Acquired for a research image collection, with no referral diagnosis — 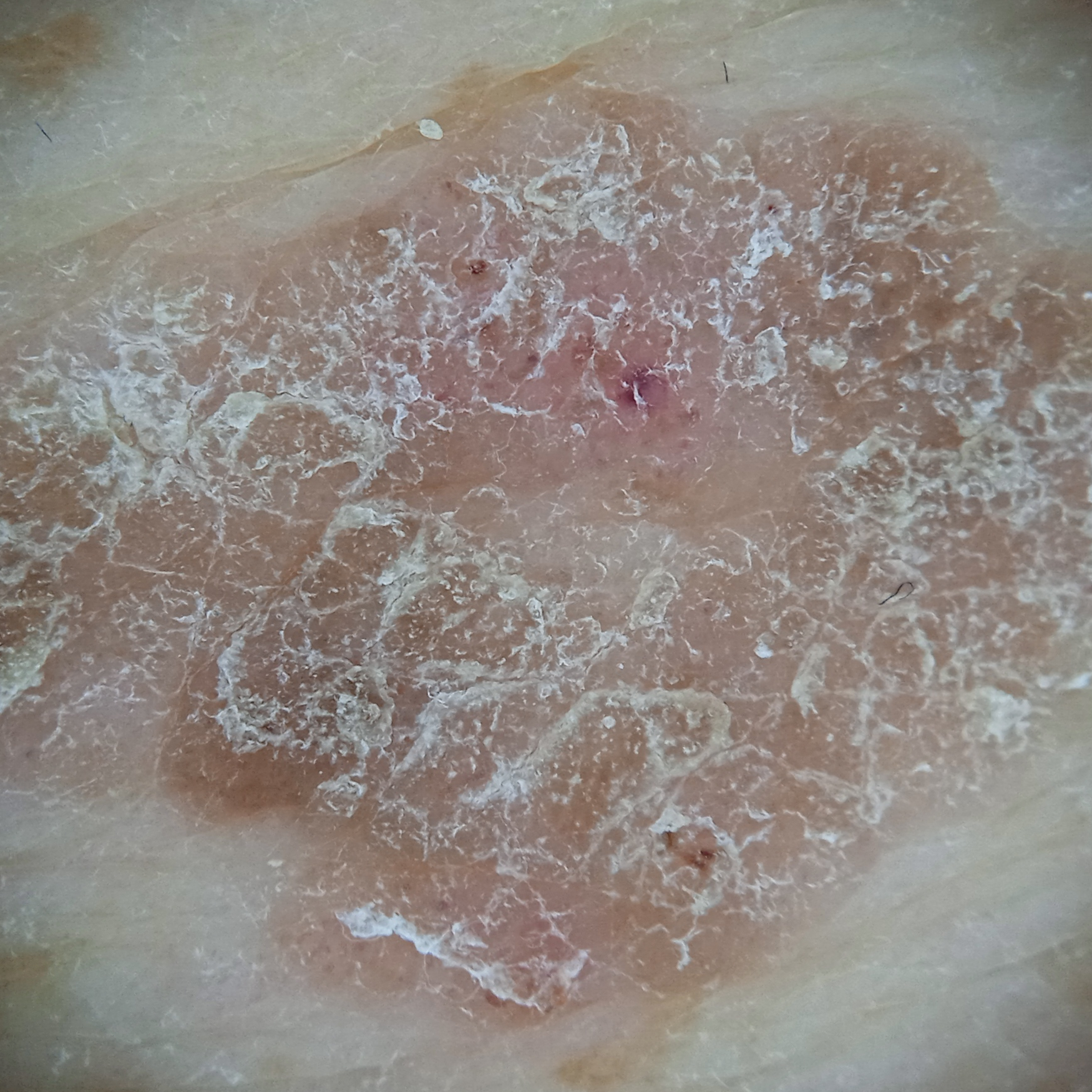{
  "lesion_location": "the back",
  "lesion_size": {
    "diameter_mm": 16.5
  },
  "diagnosis": {
    "name": "seborrheic keratosis",
    "malignancy": "benign"
  }
}